A dermoscopic close-up of a skin lesion.
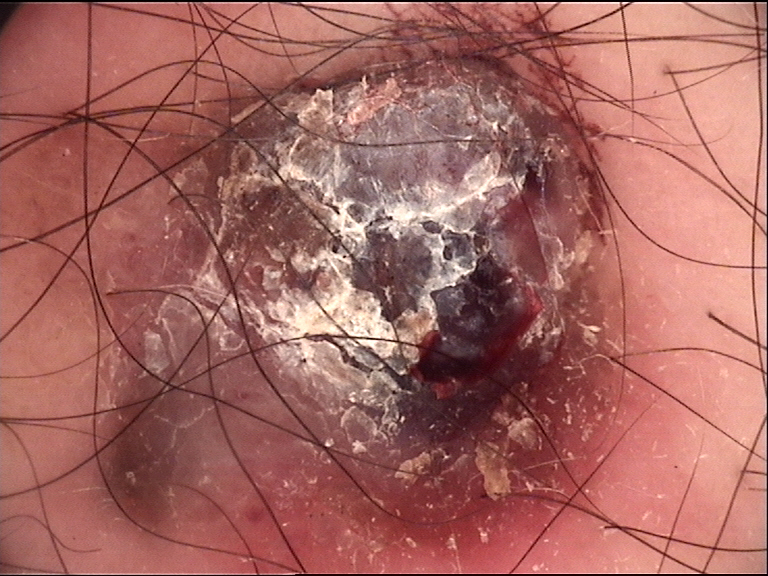Q: What is the diagnosis?
A: melanoma (biopsy-proven)